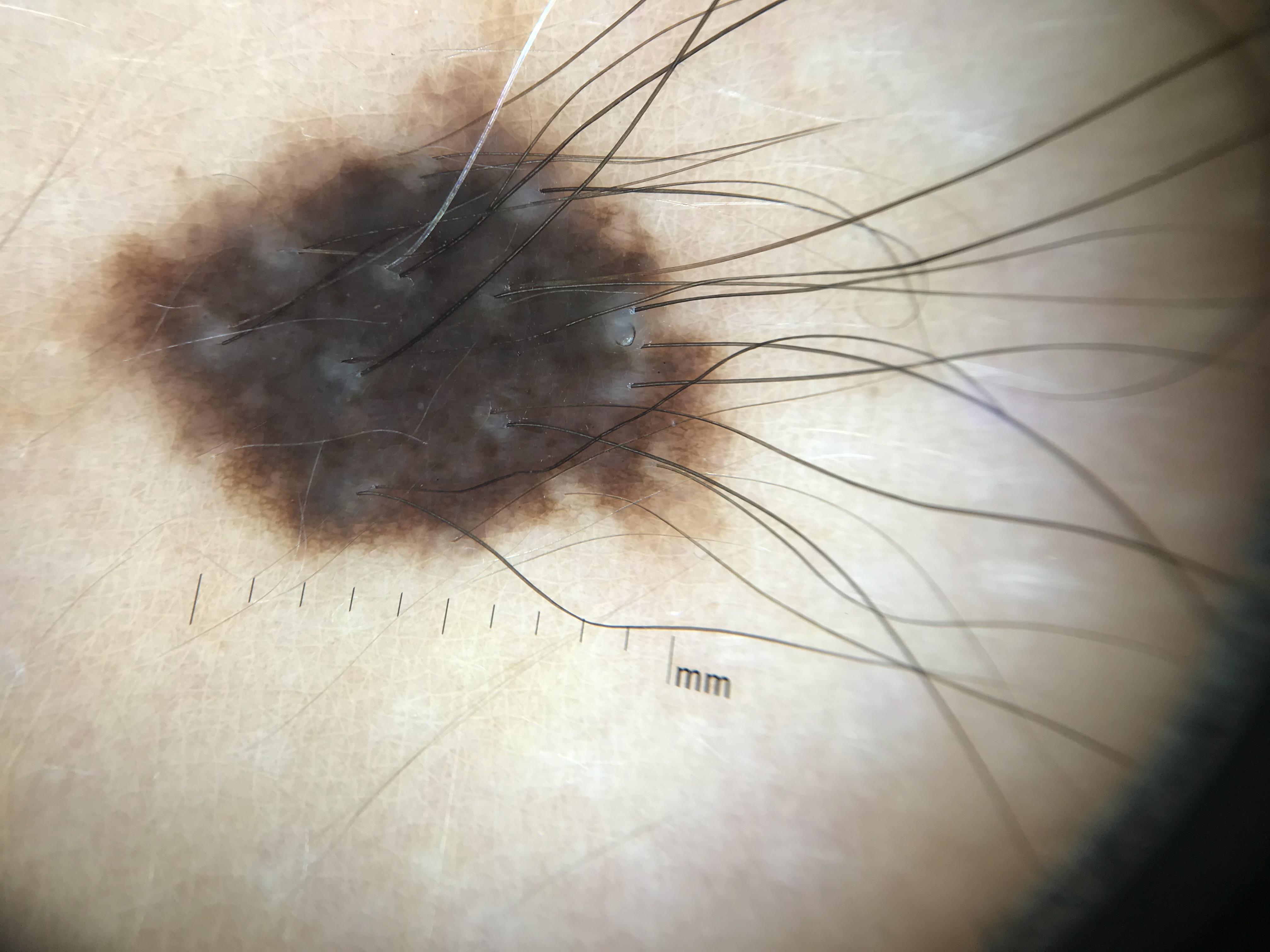class = congenital dysplastic compound nevus (expert consensus).